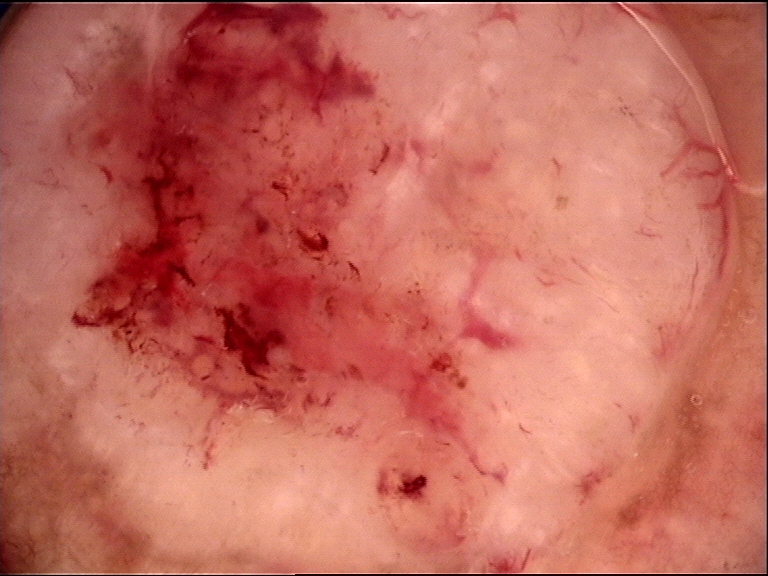A dermoscopic image of a skin lesion.
Histopathologically confirmed as a malignant, keratinocytic lesion — a basal cell carcinoma.